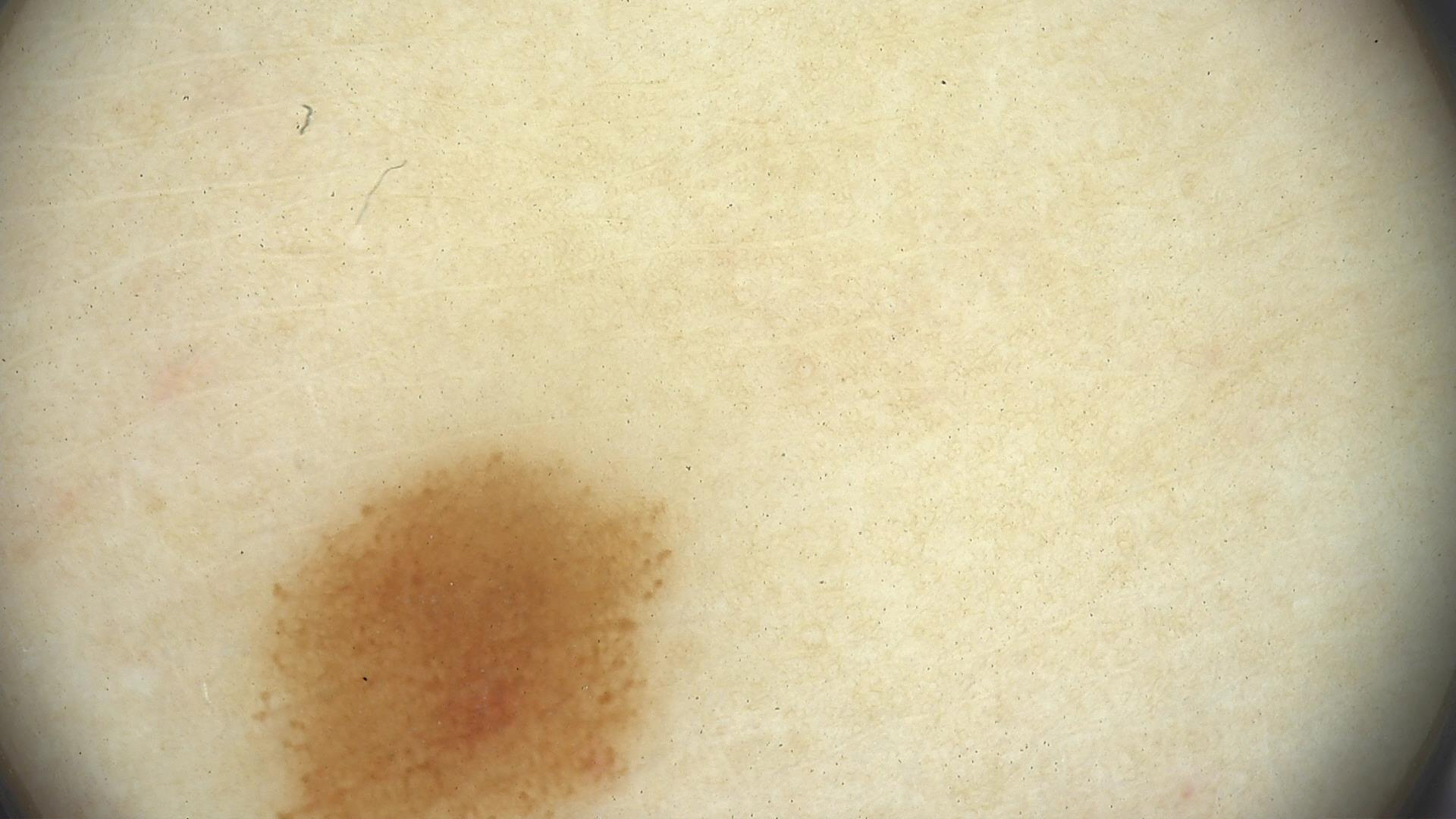{
  "image": "dermoscopy",
  "diagnosis": {
    "name": "dysplastic junctional nevus",
    "code": "jd",
    "malignancy": "benign",
    "super_class": "melanocytic",
    "confirmation": "expert consensus"
  }
}